A female patient, roughly 45 years of age; a dermoscopic image of a skin lesion.
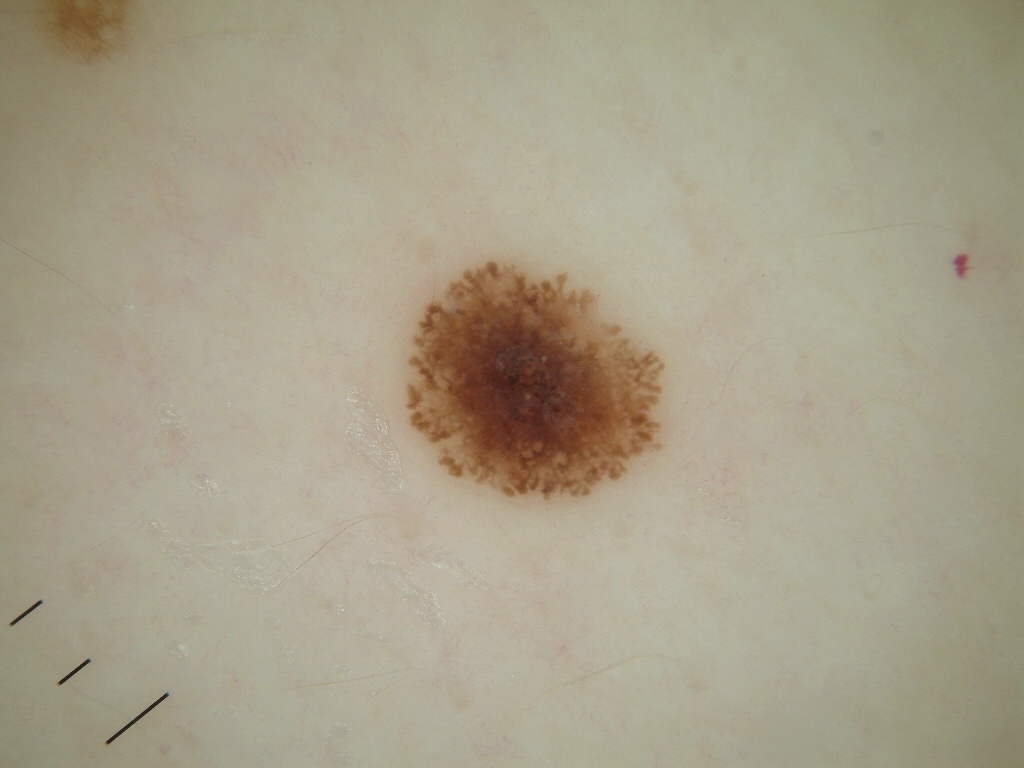Image and clinical context: The lesion occupies roughly 7% of the field. The lesion spans box(395, 253, 671, 506). The dermoscopic pattern shows pigment network and globules. Diagnosis: Histopathology confirmed a melanoma, a malignant lesion.